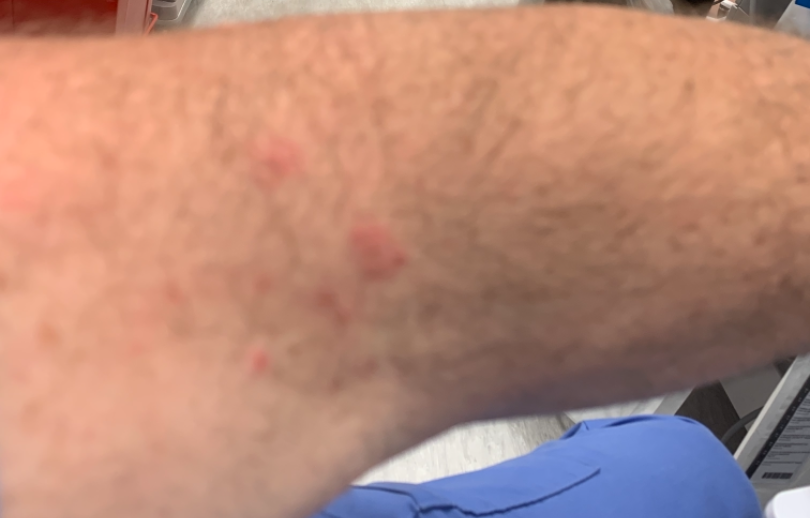An image taken at a distance.
The differential, in no particular order, includes Herpes Zoster and Allergic Contact Dermatitis.